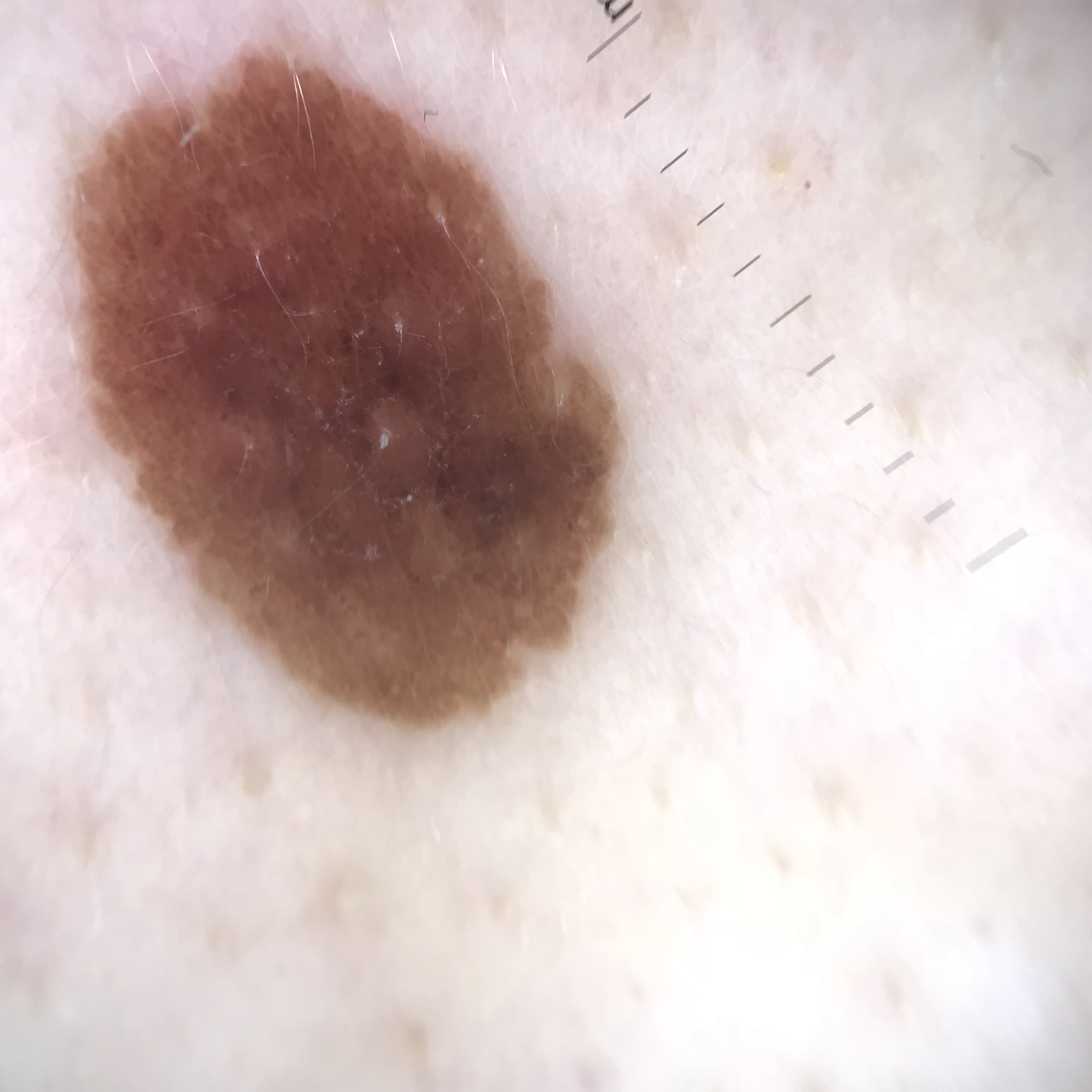Case: Dermoscopy of a skin lesion. Impression: Classified as a dysplastic junctional nevus.